A female subject in their mid-80s or older — 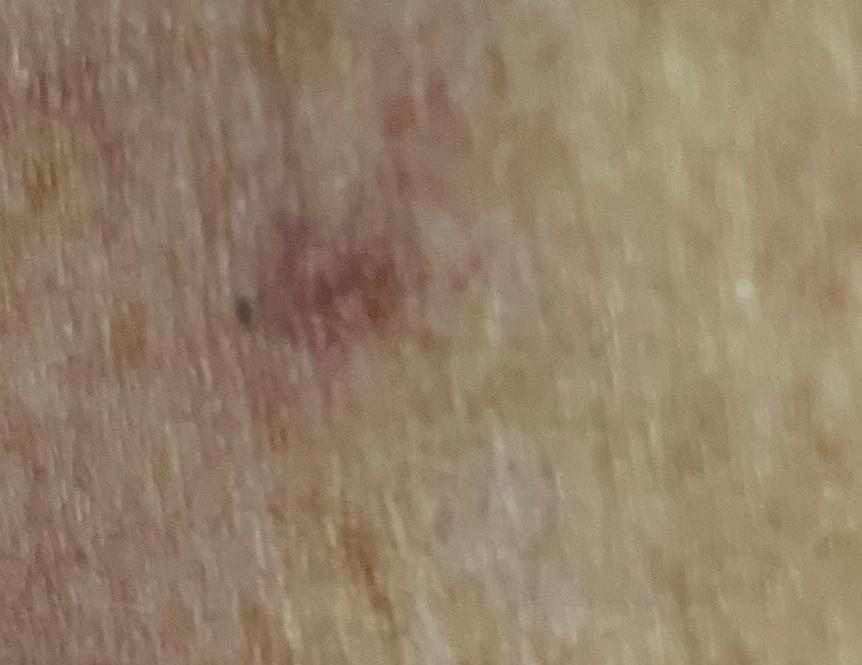diagnostic label: Basal cell carcinoma (biopsy-proven).